The patient is 40–49, female. The palm is involved. A close-up photograph — 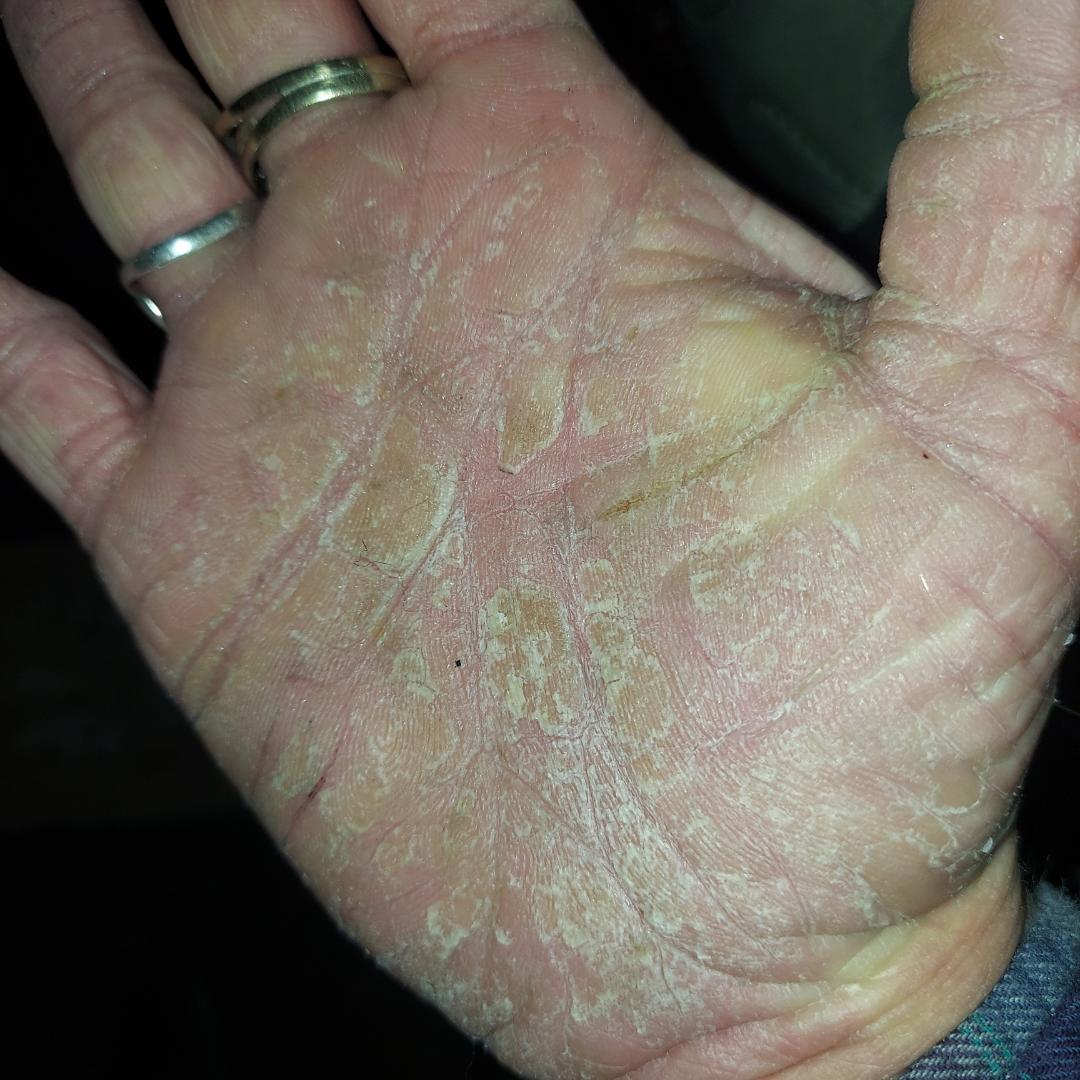{"duration": "more than one year", "texture": "rough or flaky", "skin_tone": {"fitzpatrick": "II", "monk_skin_tone": [2, 4]}, "patient_category": "a rash", "symptoms": ["pain", "bleeding", "itching", "bothersome appearance"], "differential": {"leading": ["Eczema"], "considered": ["Hyperkeratosis"], "unlikely": ["Keratoderma"]}}